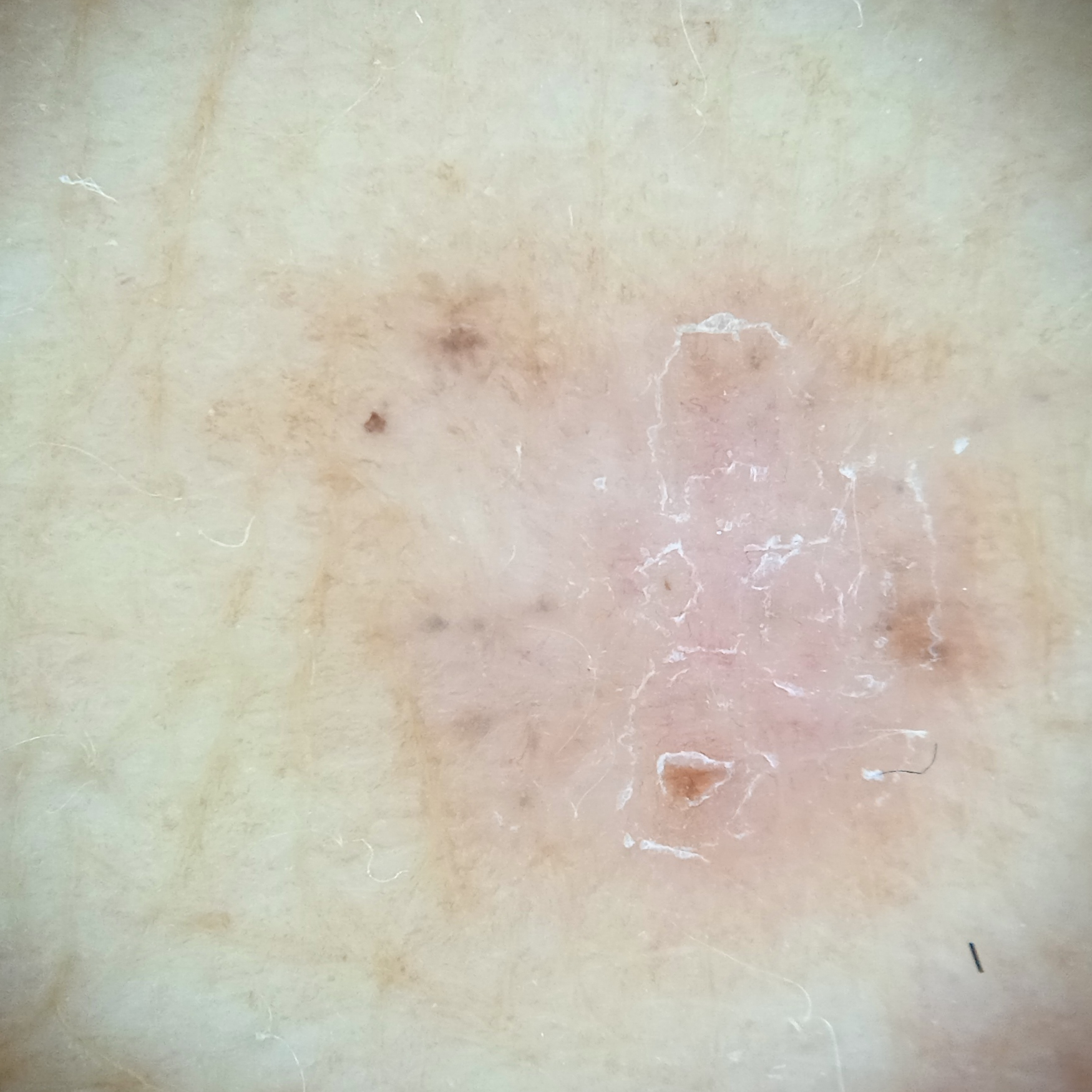Summary: A skin lesion imaged with a dermatoscope. The referring clinician suspected basal cell carcinoma. A moderate number of moles by the patient's own estimate. The patient says their skin tans without first burning. A female subject 64 years of age. The patient reports a family history of skin cancer, a personal history of cancer, and no immunosuppression. The lesion is located on the torso. Measuring roughly 8.1 mm. Conclusion: On biopsy, the diagnosis was a basal cell carcinoma, following a punch biopsy, with tumor thickness 0.6 mm.